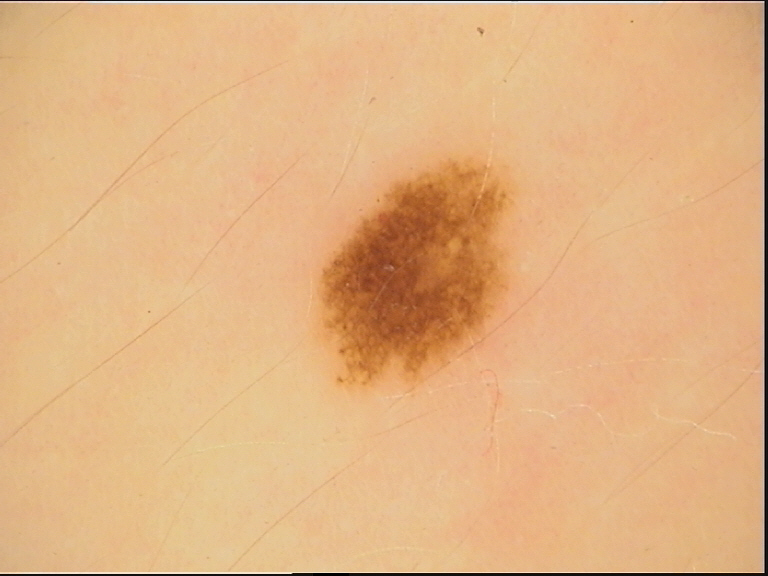* modality: dermatoscopy
* assessment: dysplastic junctional nevus (expert consensus)